A skin lesion imaged with a dermatoscope.
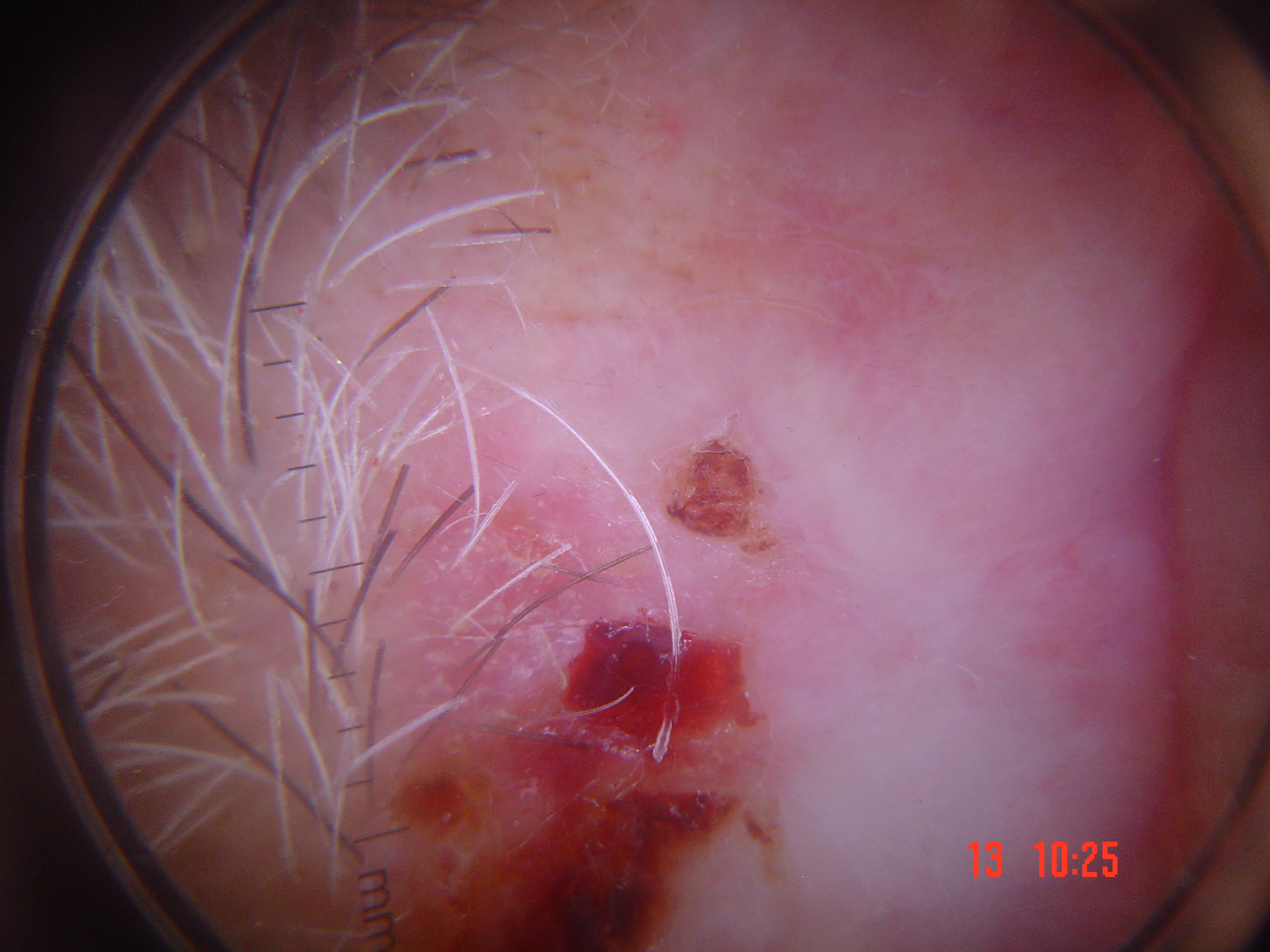Histopathologically confirmed as a keratinocytic lesion — a squamous cell carcinoma.